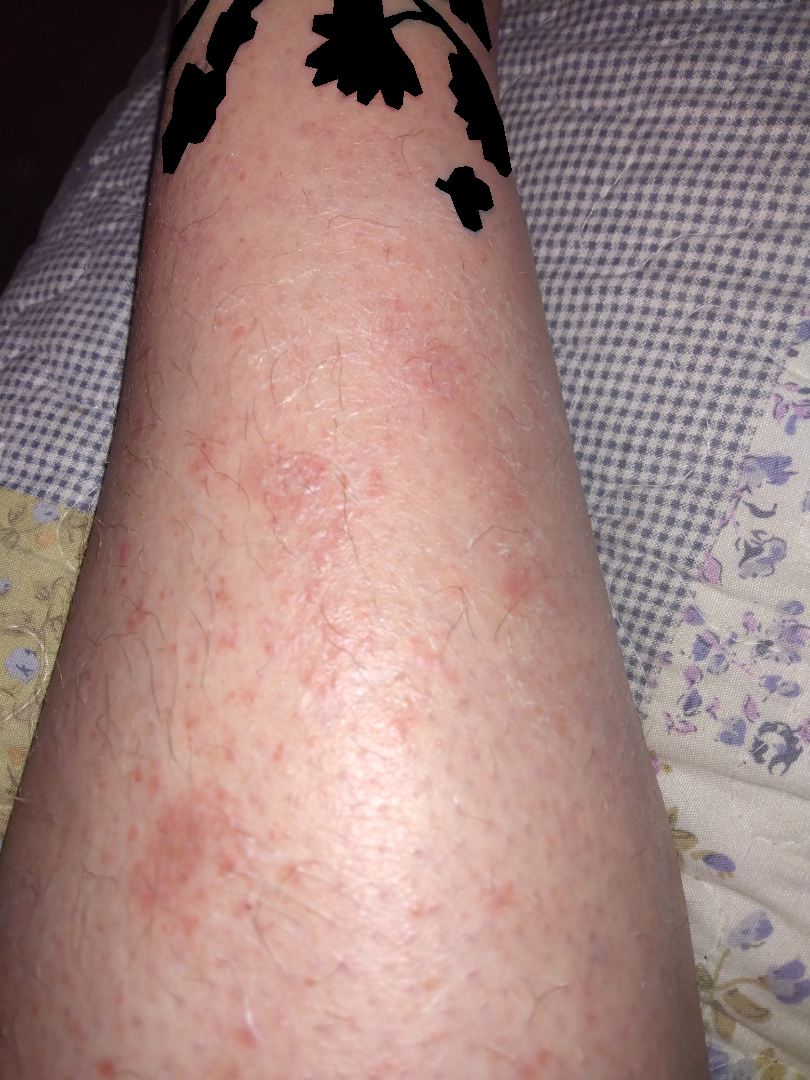| feature | finding |
|---|---|
| diagnostic considerations | Eczema (0.67); Allergic Contact Dermatitis (0.33) |